This image was taken at a distance, the affected area is the leg and top or side of the foot — 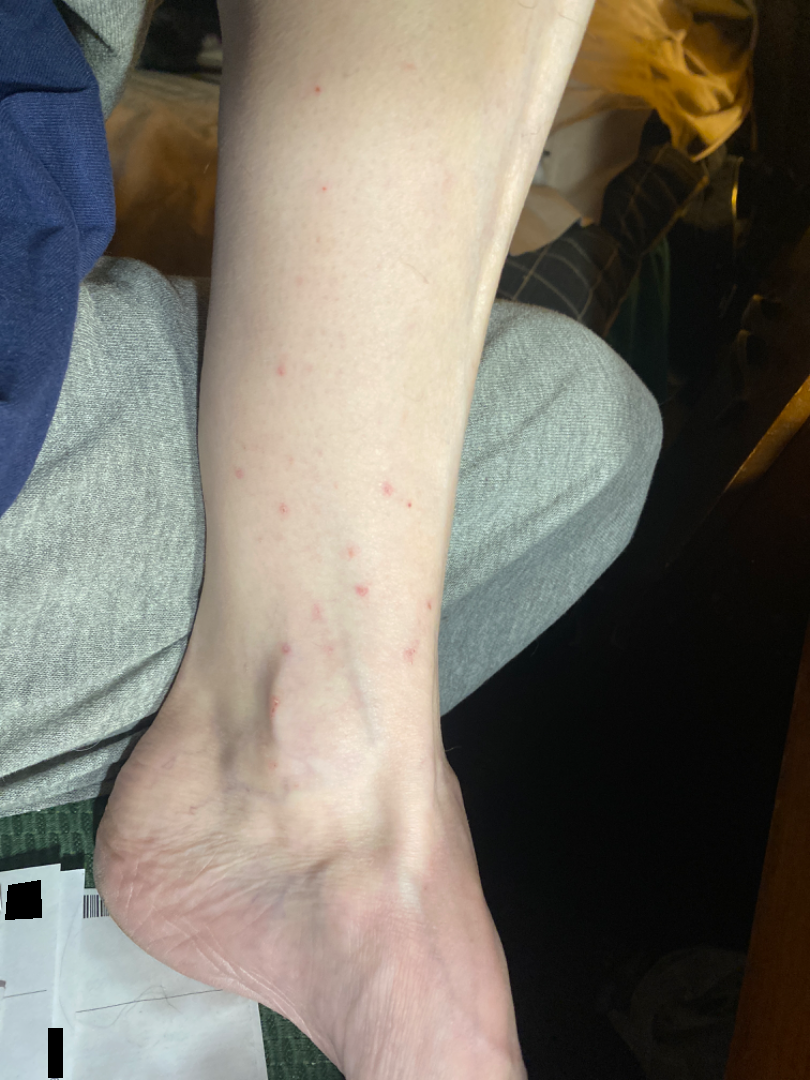Review:
Single-reviewer assessment: favoring Eczema; also raised was Hypersensitivity.